Located on the leg; the photograph is a close-up of the affected area: 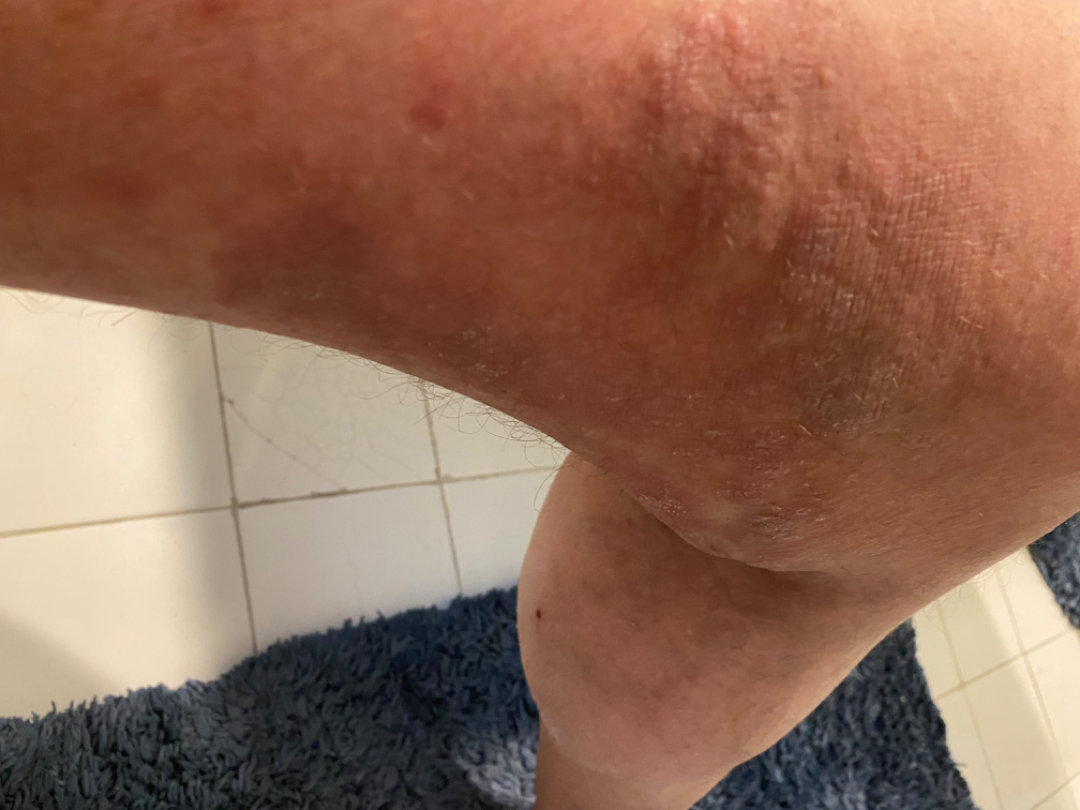<summary>
  <assessment>not assessable</assessment>
  <skin_tone>
    <fitzpatrick>IV</fitzpatrick>
  </skin_tone>
  <duration>one to four weeks</duration>
  <texture>rough or flaky</texture>
</summary>